A dermoscopic close-up of a skin lesion:
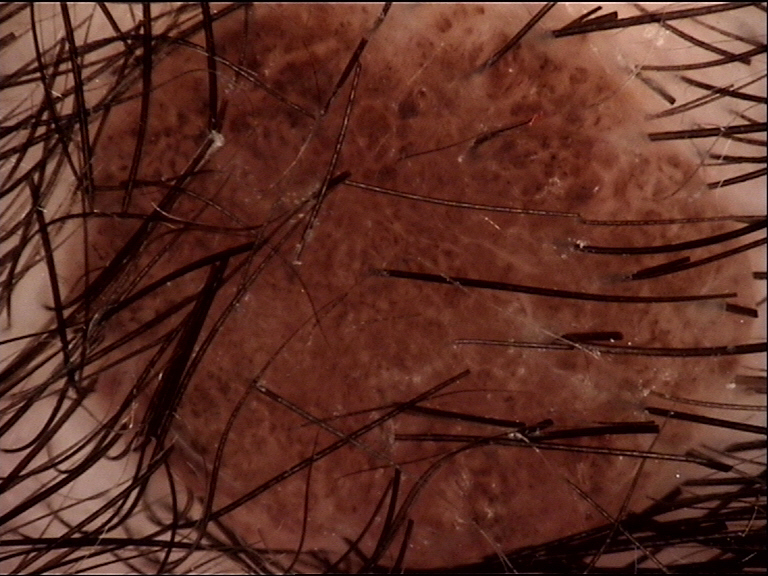– diagnostic label · dermal nevus (expert consensus)